The photograph was taken at a distance · the lesion involves the arm, top or side of the foot, palm and back of the hand · female contributor, age 40–49:
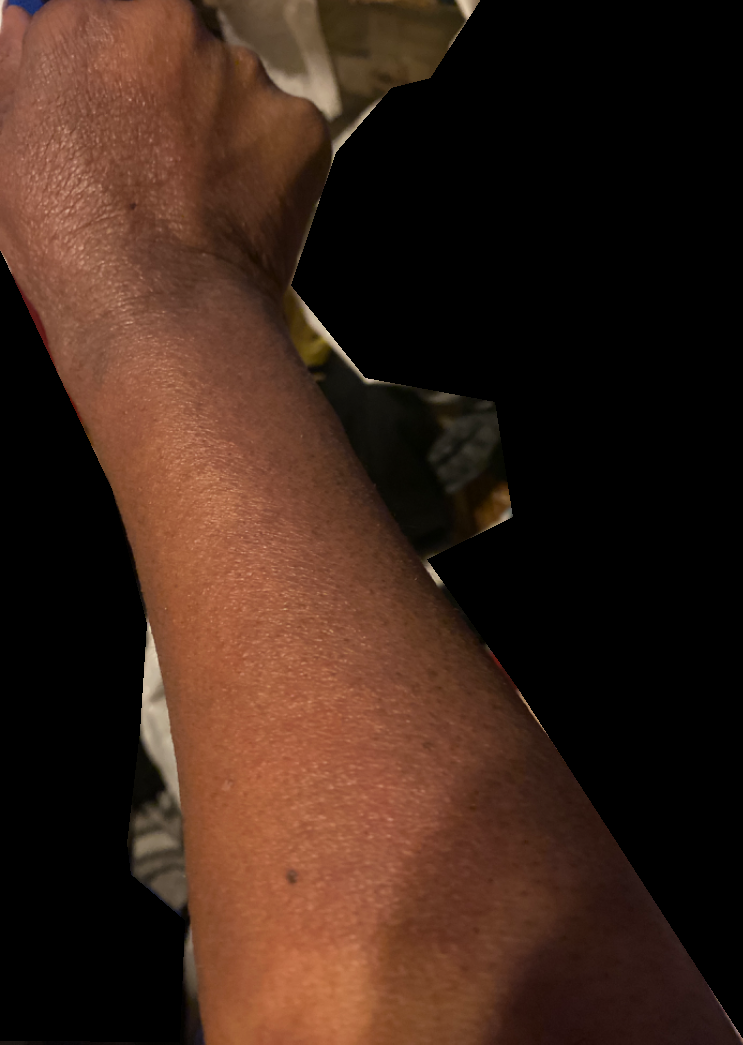History:
The patient described the issue as a rash. The patient reports enlargement, burning, itching, bleeding and darkening. The patient reports the lesion is rough or flaky. Reported duration is one to three months. No associated systemic symptoms reported.
Impression:
On independent review by the dermatologists, most consistent with Acute and chronic dermatitis.